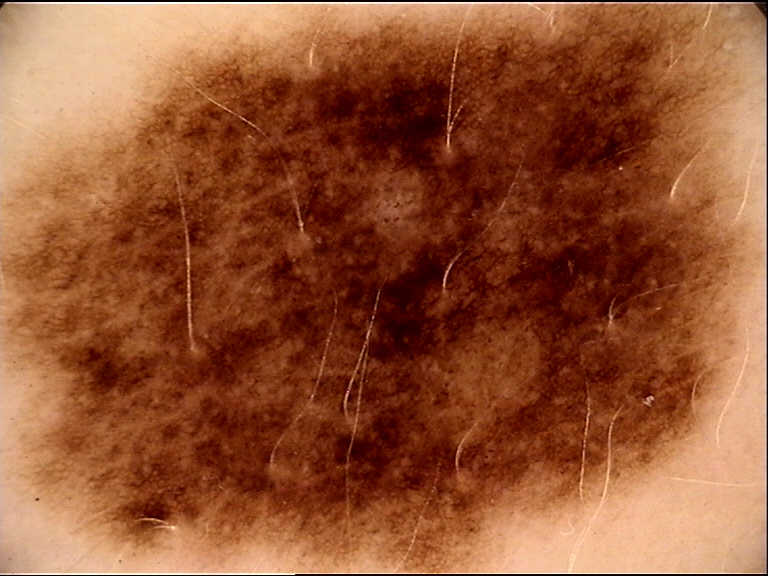image=dermoscopy; label=dysplastic compound nevus (expert consensus).